The subject is male. This is a close-up image. The affected area is the front of the torso and back of the torso: 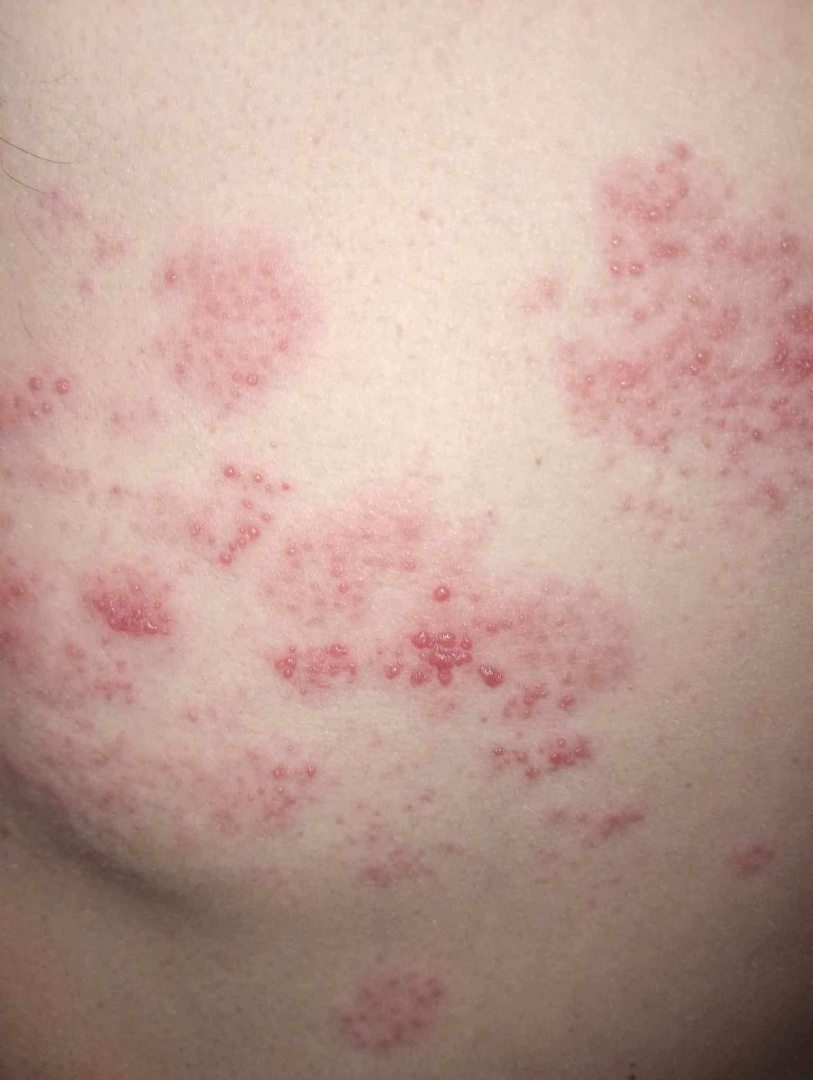On photographic review by a dermatologist: the impression is Herpes Zoster.